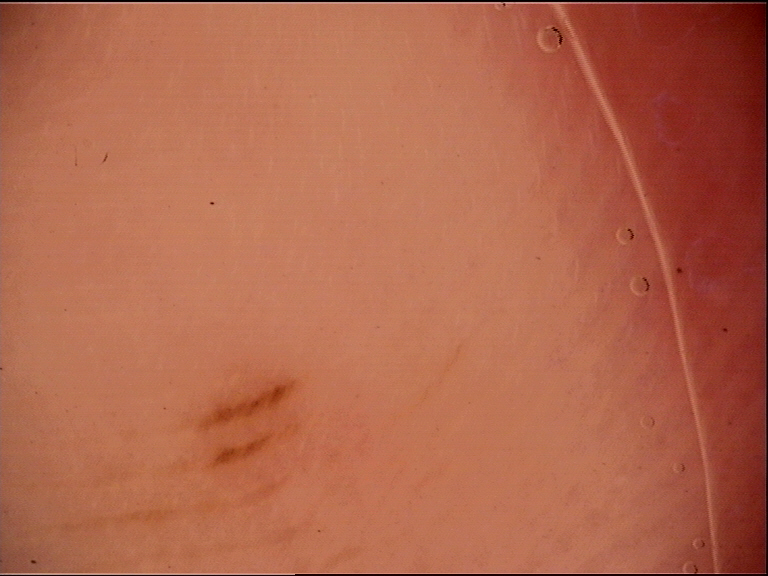Dermoscopy of a skin lesion.
The architecture is that of a banal lesion.
Labeled as an acral junctional nevus.